The patient says their skin reddens with sun exposure. The patient reports a history of sunbed use. Acquired for a research image collection, with no referral diagnosis. The patient describes having numerous moles. A female patient age 26.
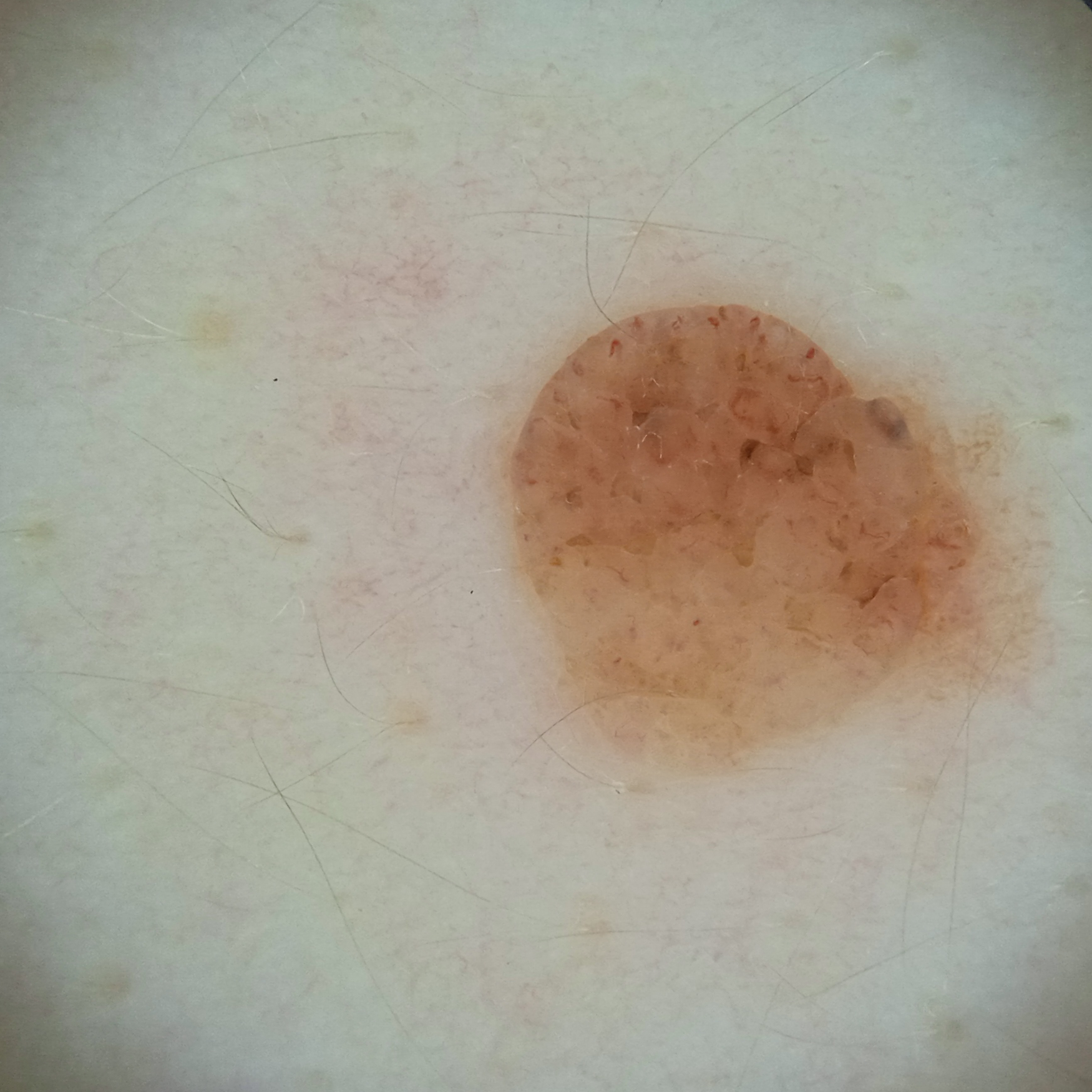The lesion is on the back.
The dermatologists' assessment was a melanocytic nevus.